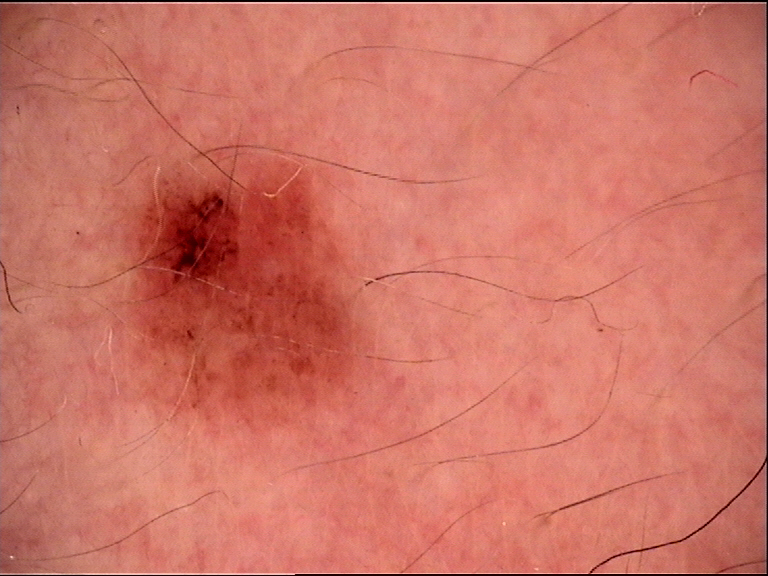{
  "image": "dermoscopy",
  "diagnosis": {
    "name": "dysplastic junctional nevus",
    "code": "jd",
    "malignancy": "benign",
    "super_class": "melanocytic",
    "confirmation": "expert consensus"
  }
}